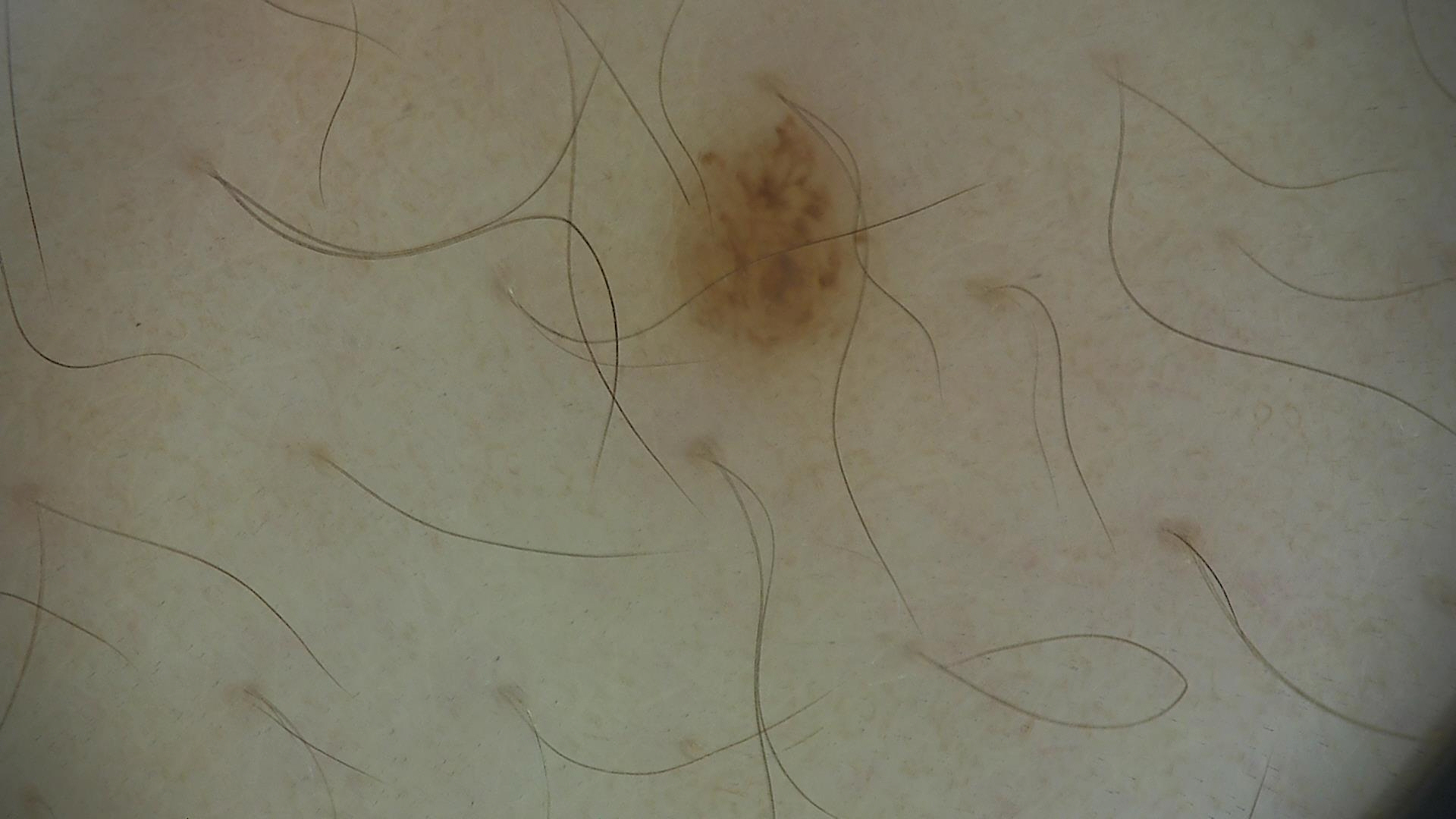Q: What kind of image is this?
A: dermoscopy
Q: What is this lesion?
A: dysplastic junctional nevus (expert consensus)